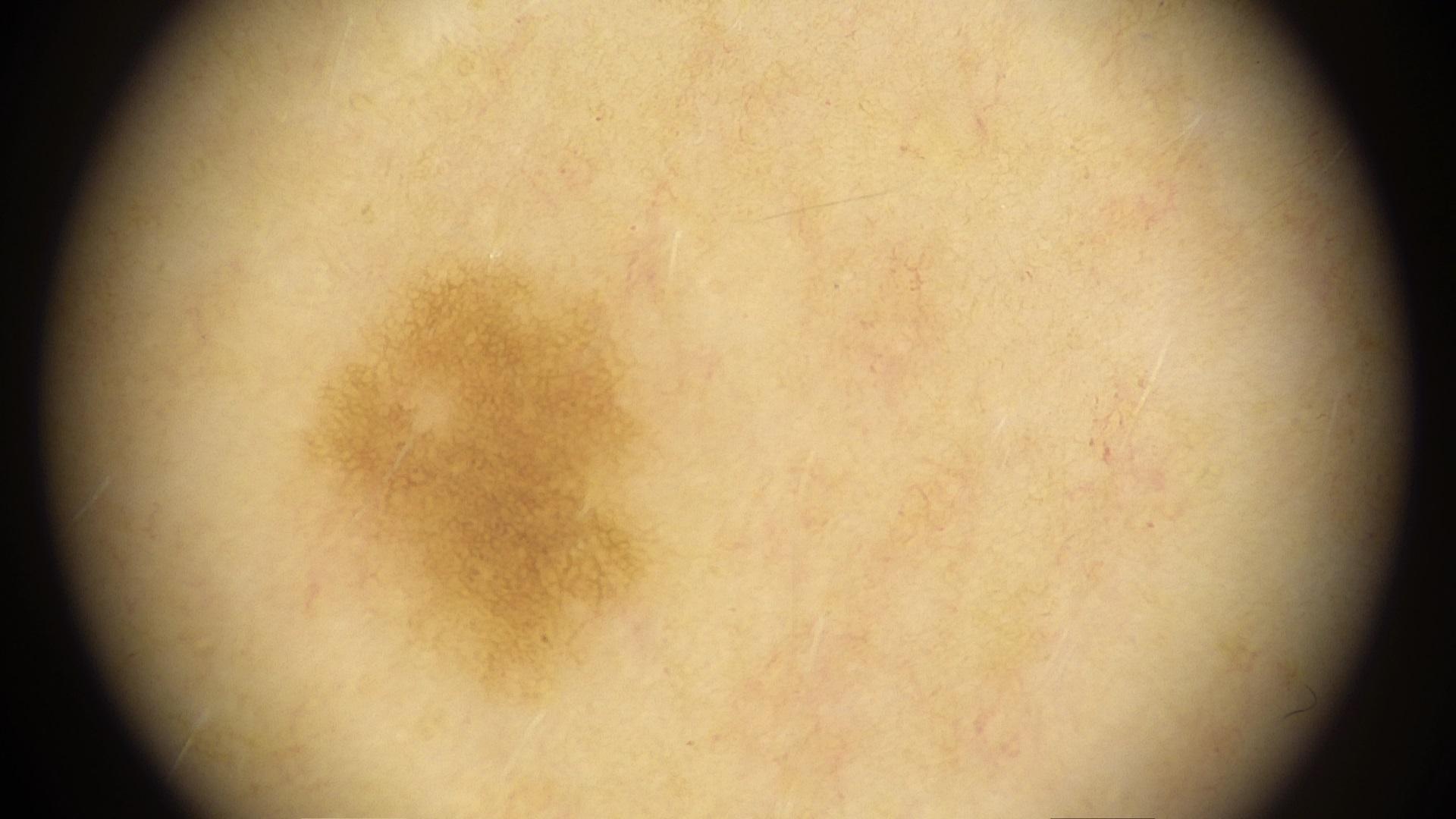A contact-polarized dermoscopy image of a skin lesion.
Expert review favored a nevus.